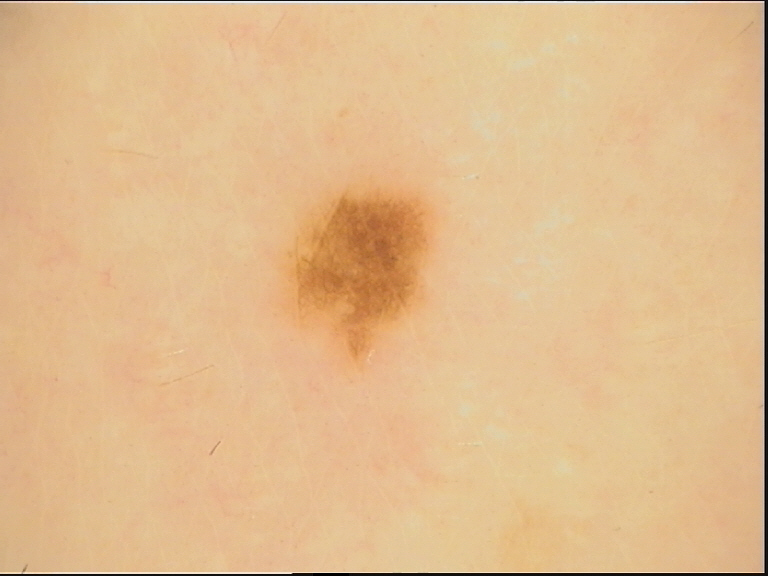image type: dermoscopy, subtype: banal, diagnosis: junctional nevus (expert consensus).